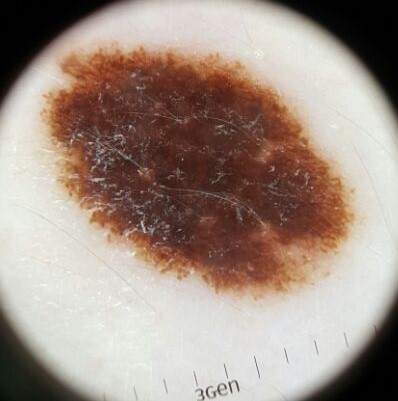The diagnostic label was a dysplastic compound nevus.